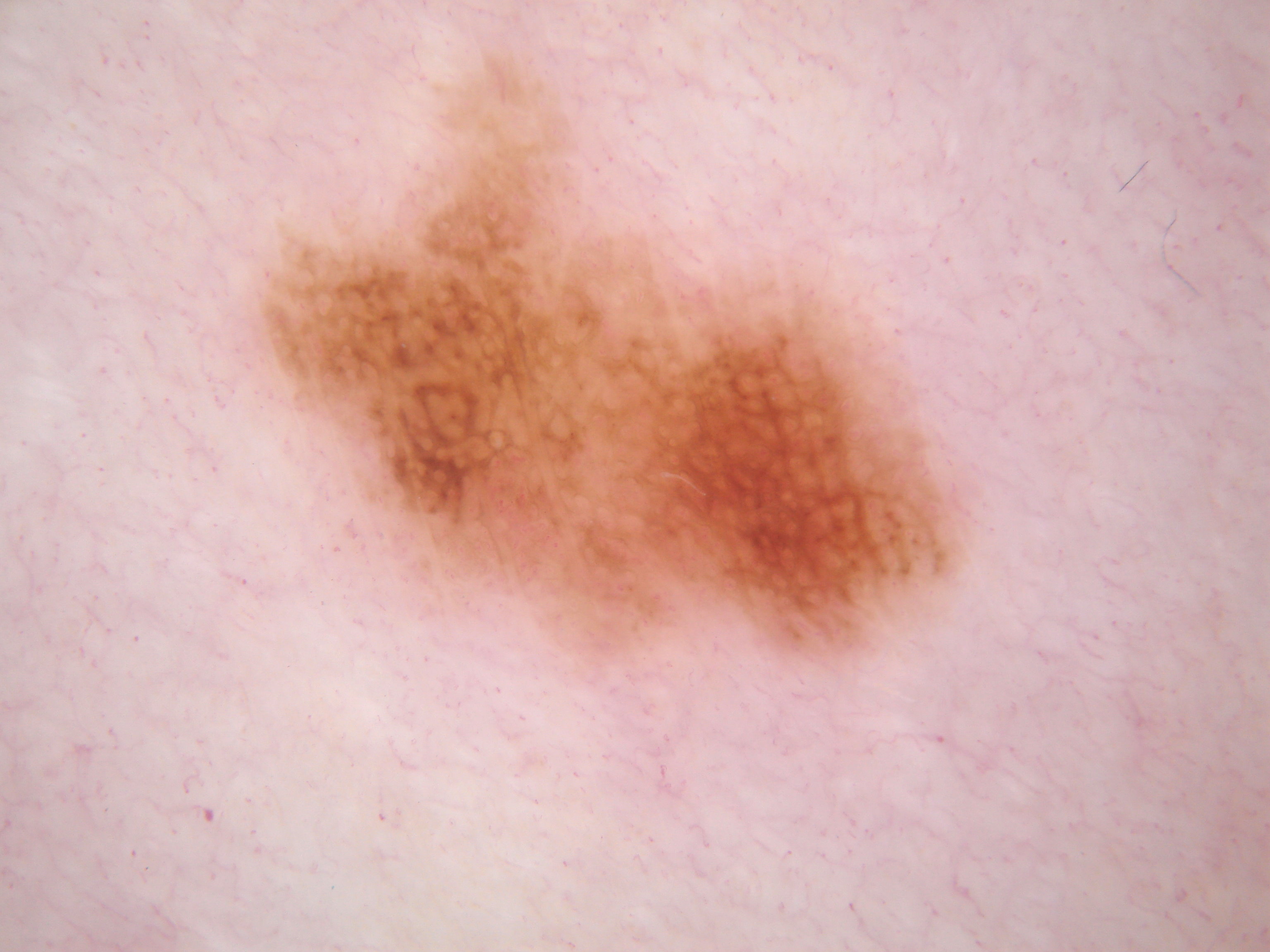Image and clinical context: A dermoscopic view of a skin lesion. A mid-sized lesion within the field. Dermoscopic review identifies pigment network. In (x1, y1, x2, y2) order, the visible lesion spans bbox=[224, 28, 1006, 700]. Conclusion: Histopathologically confirmed as a melanoma.